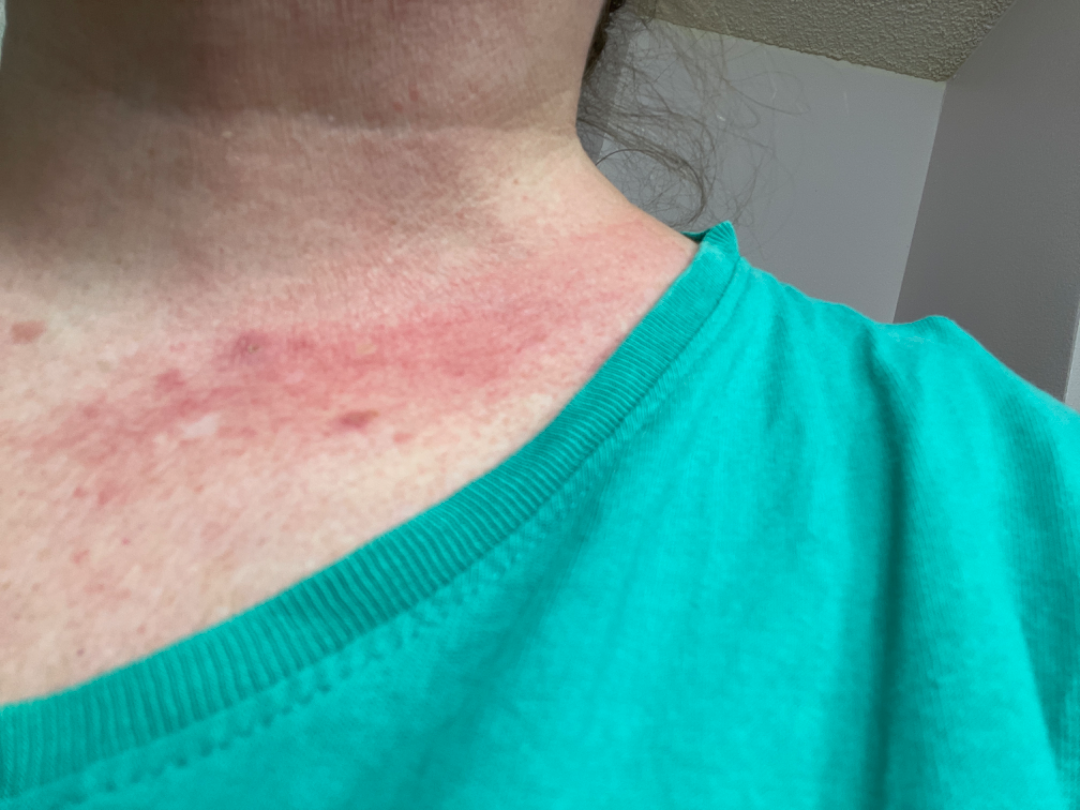The affected area is the front of the torso and head or neck. Reported lesion symptoms include darkening, itching and burning. A close-up photograph. Present for less than one week. On photographic review by a dermatologist: the differential is split between Folliculitis and Eczema.